The condition has been present for less than one week, the affected area is the leg, symptoms reported: itching, the subject is a female aged 60–69, the contributor reports the lesion is raised or bumpy, the patient described the issue as a rash, the photograph was taken at an angle, the contributor reports associated joint pain:
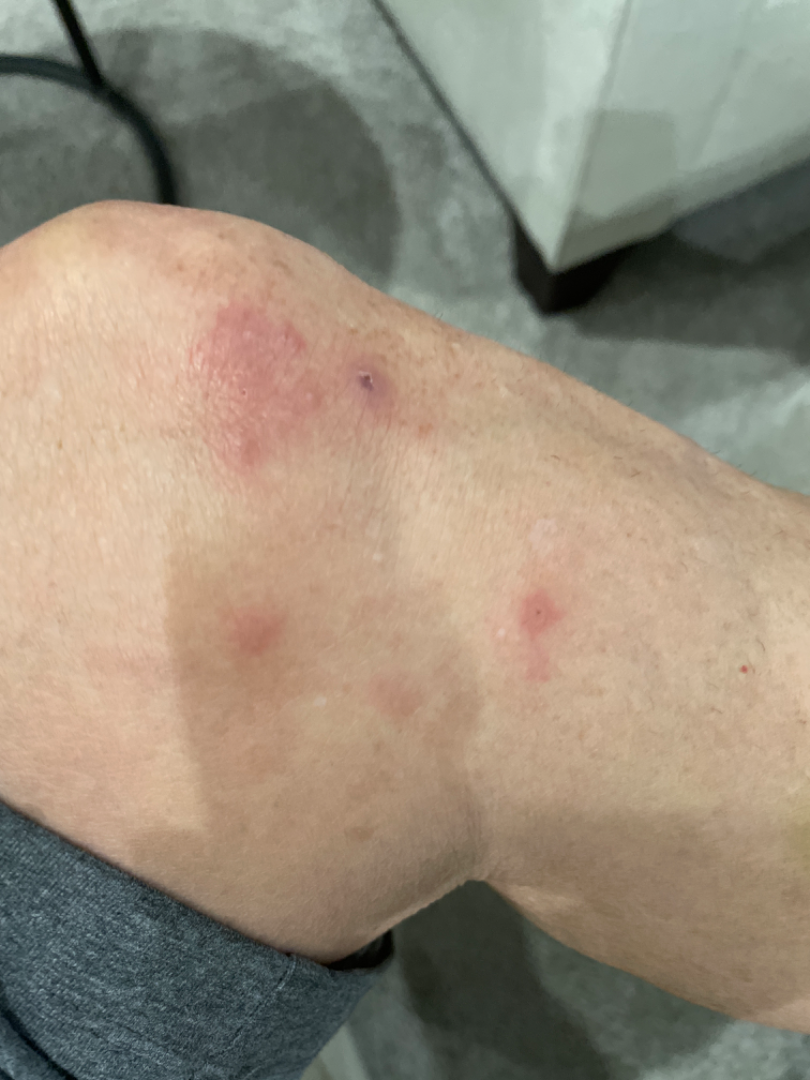| feature | finding |
|---|---|
| differential | Skin infection (considered); Folliculitis (considered); Eczema (remote) |